On a questionnaire the patient reported a personal history of skin cancer, immunosuppression, and a personal history of cancer; a clinical photograph of a skin lesion; a female patient age 72: 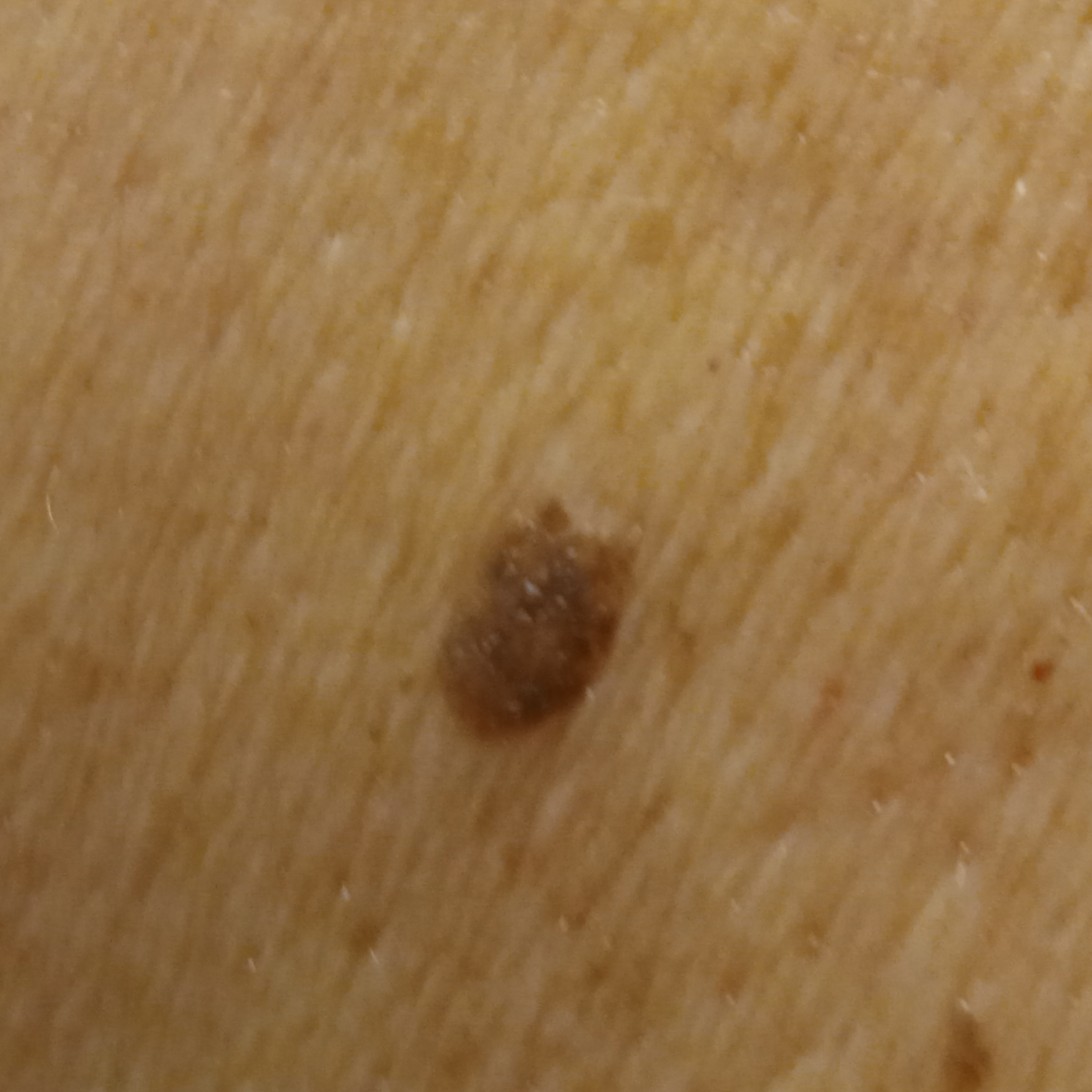{"lesion_location": "the back", "lesion_size": {"diameter_mm": 6.3}, "diagnosis": {"name": "seborrheic keratosis", "malignancy": "benign"}}